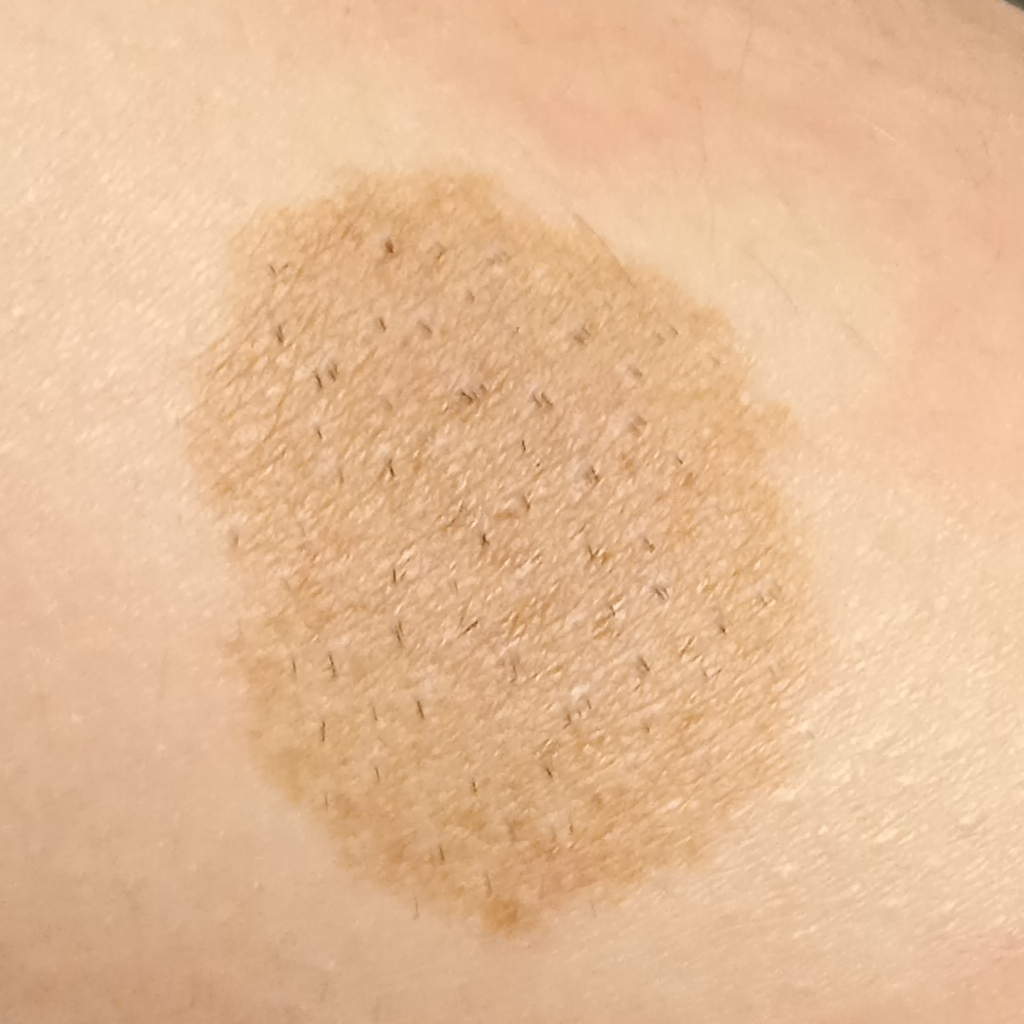nevus count — few melanocytic nevi overall | patient — male, aged 15 | modality — clinical photo | anatomic site — an arm | diameter — 26.1 mm | diagnosis — melanocytic nevus (biopsy-proven).